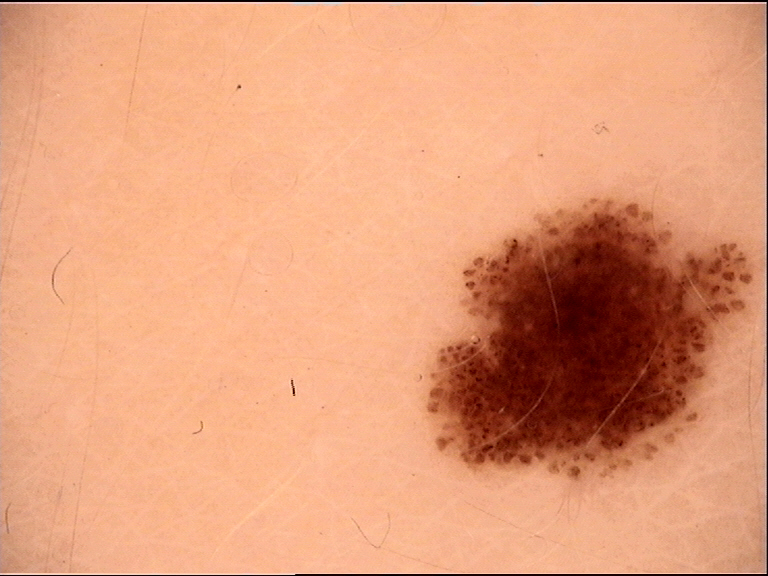<dermoscopy>
<lesion_type>
<main_class>banal</main_class>
<pattern>junctional</pattern>
</lesion_type>
<diagnosis>
<name>junctional nevus</name>
<code>jb</code>
<malignancy>benign</malignancy>
<super_class>melanocytic</super_class>
<confirmation>expert consensus</confirmation>
</diagnosis>
</dermoscopy>